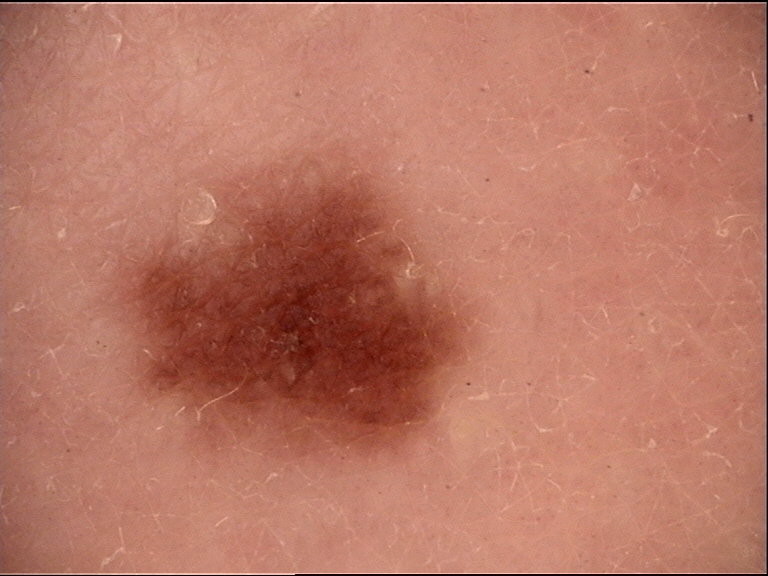{
  "image": "dermoscopy",
  "diagnosis": {
    "name": "junctional nevus",
    "code": "jb",
    "malignancy": "benign",
    "super_class": "melanocytic",
    "confirmation": "expert consensus"
  }
}